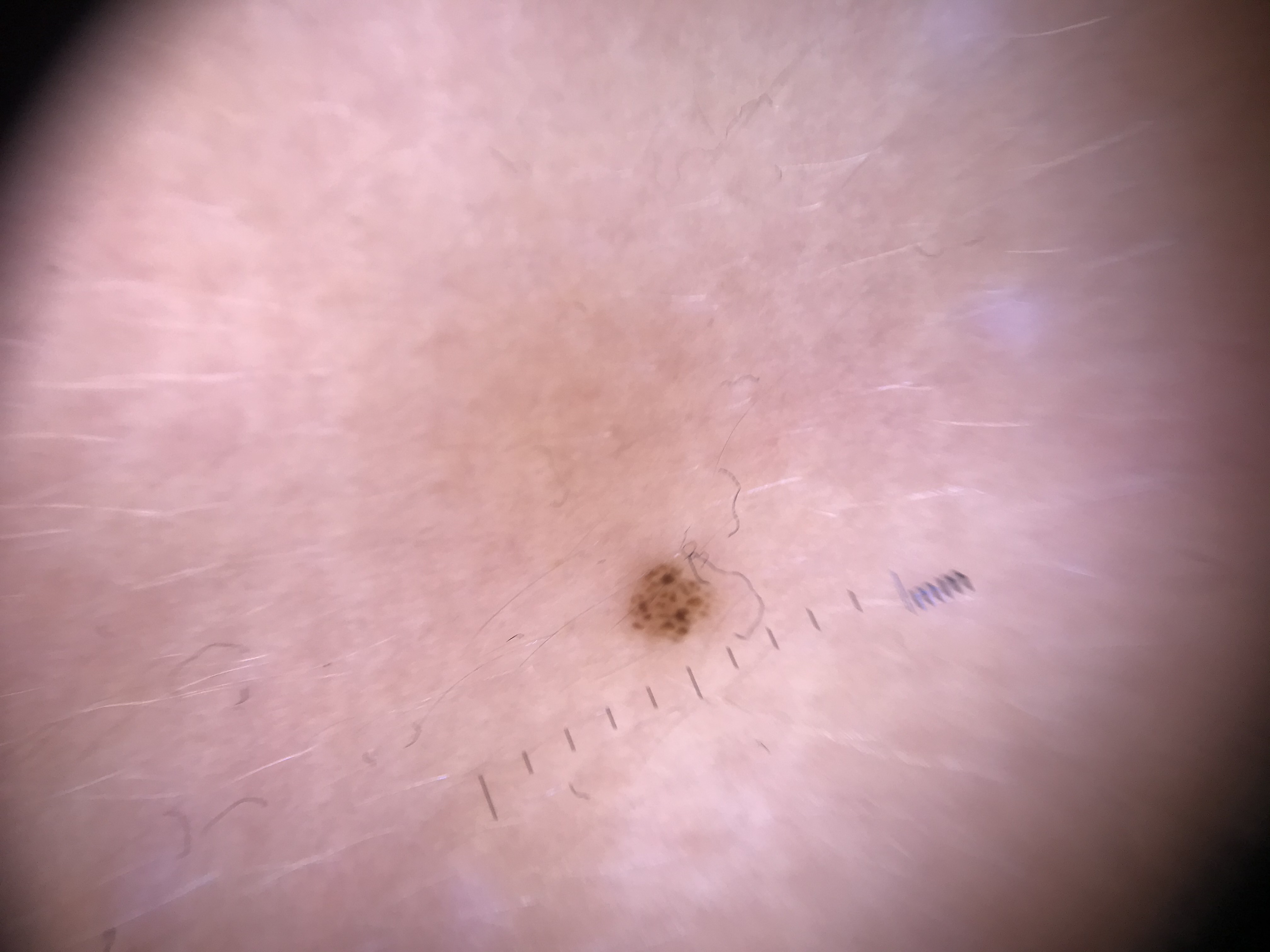<dermoscopy>
  <image>dermatoscopy</image>
  <diagnosis>
    <name>junctional nevus</name>
    <code>jb</code>
    <malignancy>benign</malignancy>
    <super_class>melanocytic</super_class>
    <confirmation>expert consensus</confirmation>
  </diagnosis>
</dermoscopy>